The front of the torso, head or neck and back of the torso are involved. A close-up photograph. The patient reports the lesion is raised or bumpy and rough or flaky. Self-categorized by the patient as a rash. Reported duration is one to four weeks. Symptoms reported: bothersome appearance, itching and burning:
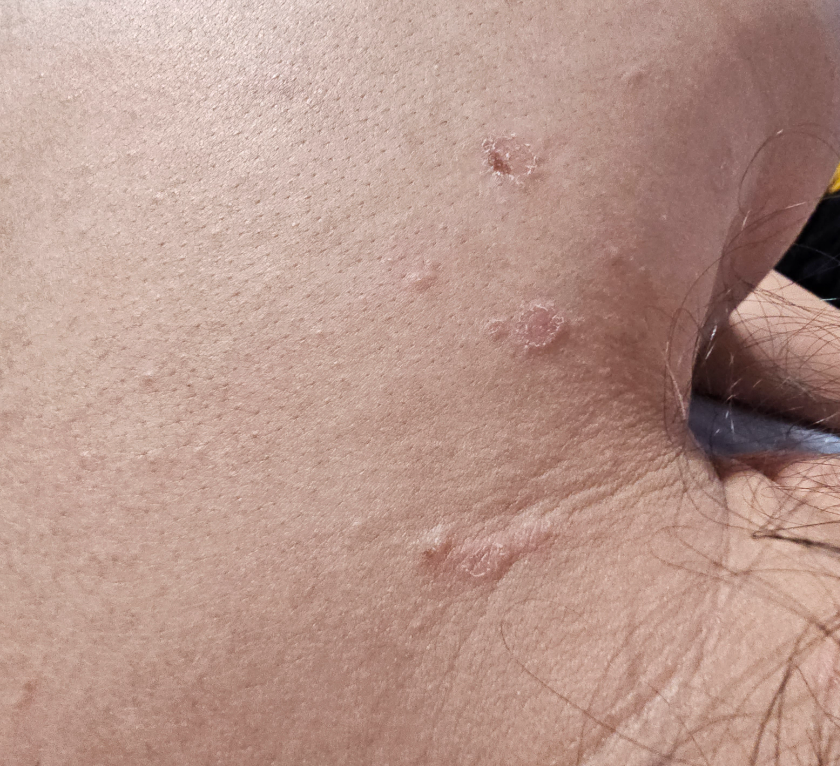The reviewer was unable to grade this case for skin condition.